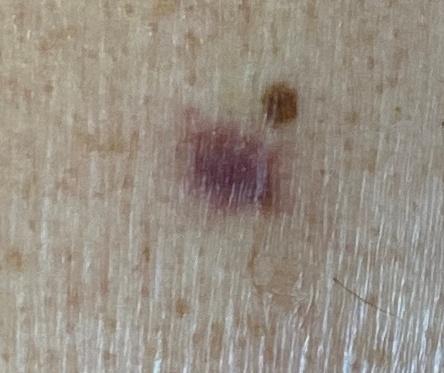Q: How was this image acquired?
A: clinical photograph
Q: What Fitzpatrick skin type was recorded?
A: II
Q: What are the patient's age and sex?
A: male, aged 73-77
Q: Where is the lesion located?
A: the trunk, specifically the posterior trunk
Q: What is the diagnosis?
A: Basal cell carcinoma (biopsy-proven)